Close-up view: 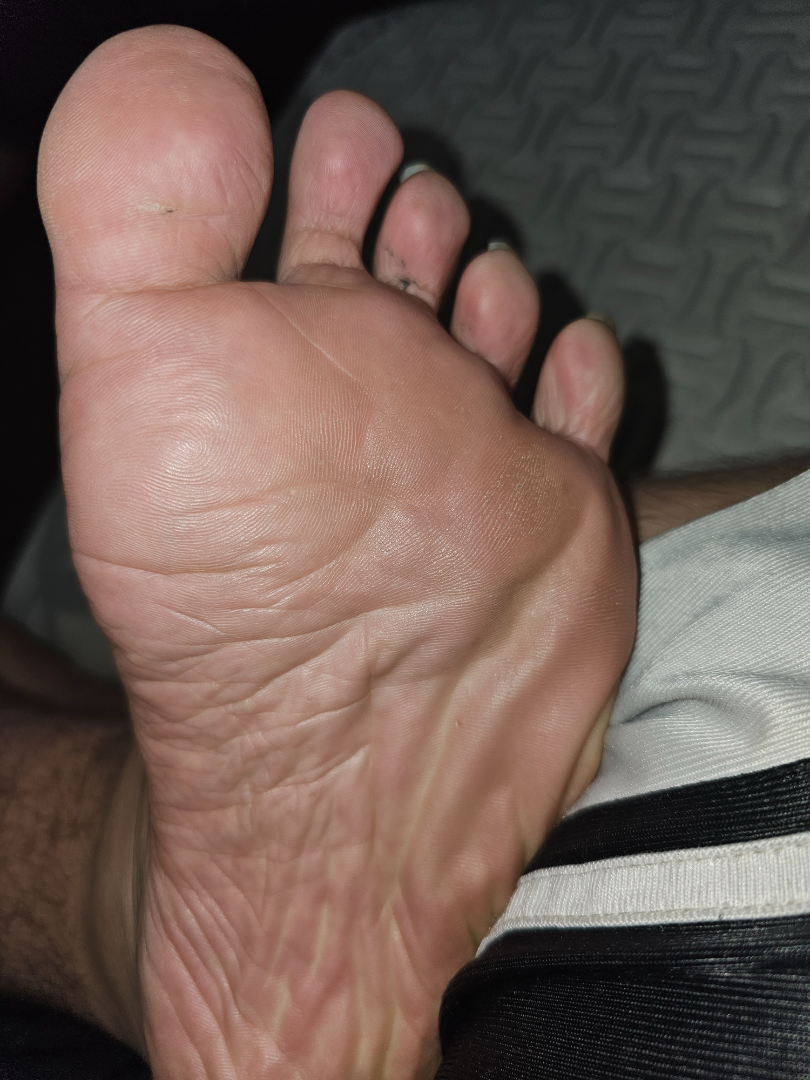assessment: no discernible pathology.